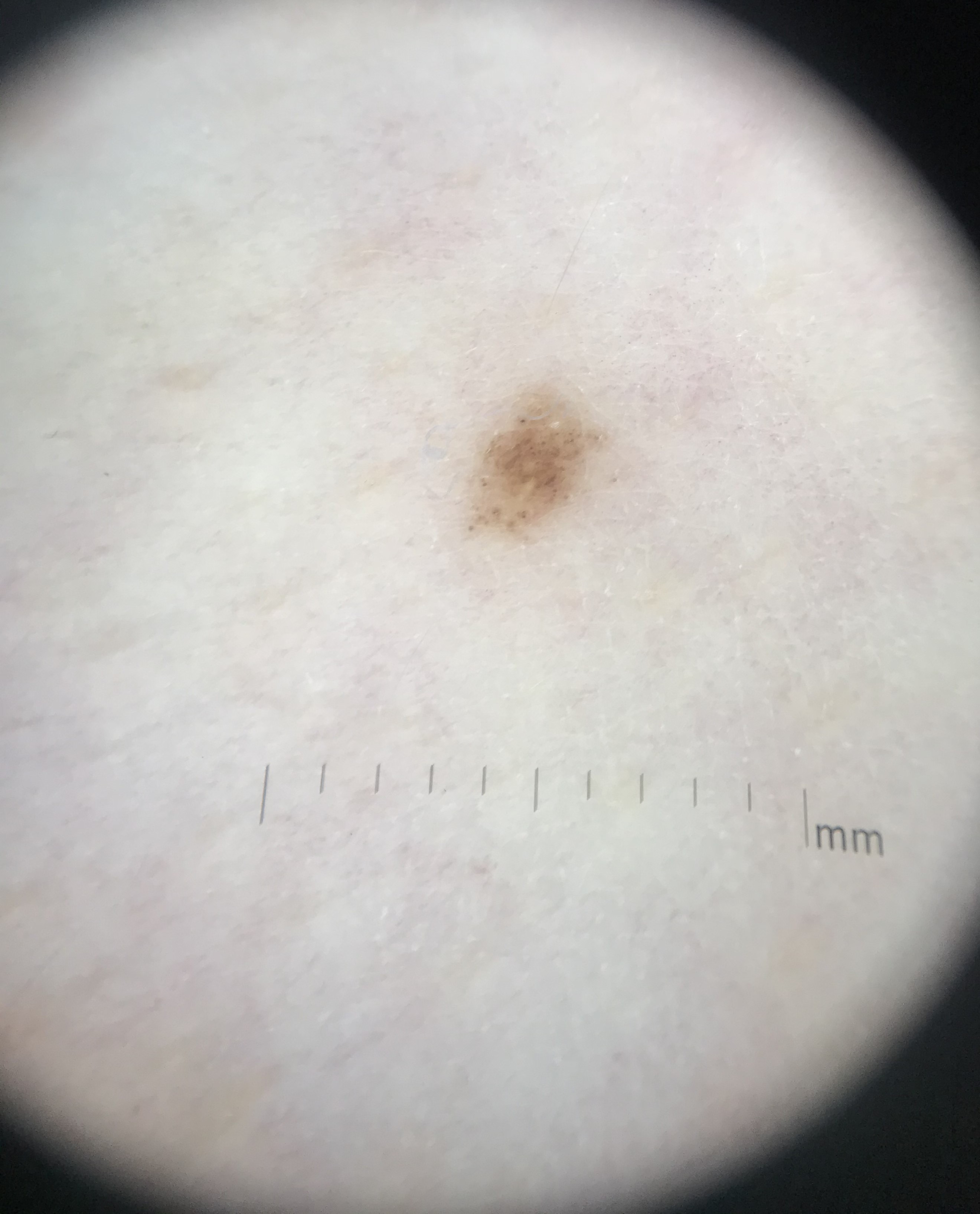The diagnosis was a dysplastic junctional nevus.